Reported duration is one to four weeks. This image was taken at a distance. The lesion involves the arm, back of the hand and leg. The contributor is 40–49, male. Reported lesion symptoms include itching and bothersome appearance. Texture is reported as rough or flaky and raised or bumpy. The patient described the issue as a rash:
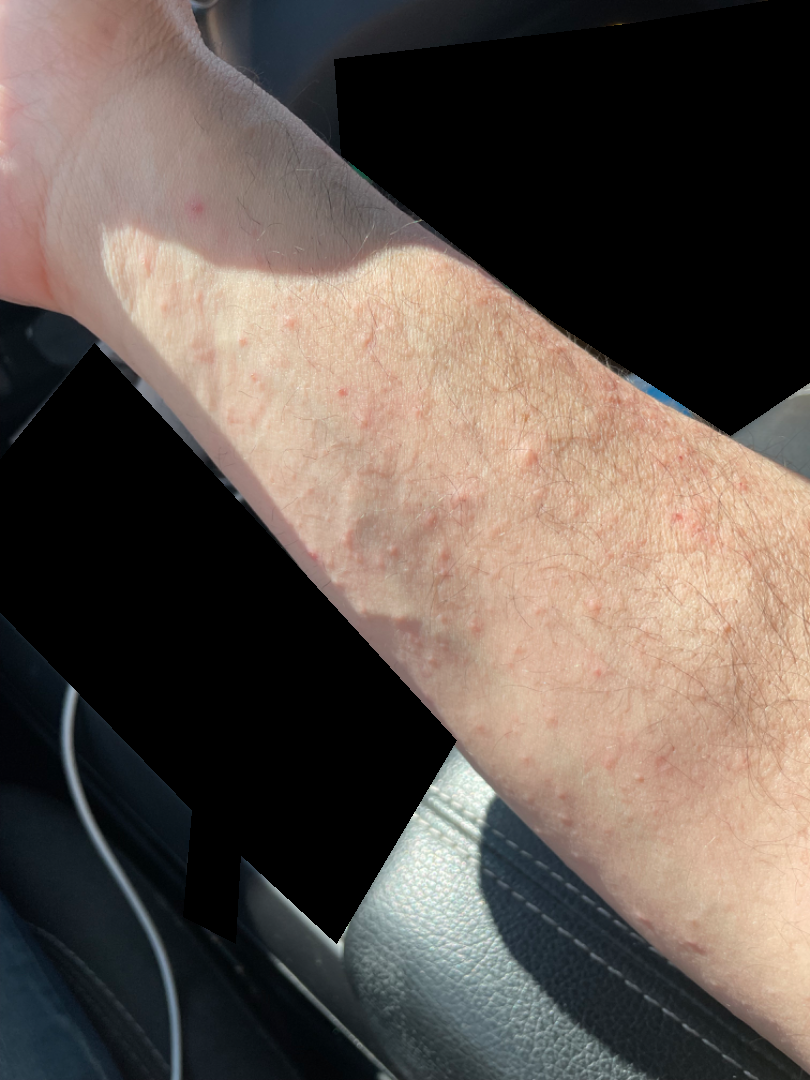dermatologist impression = Eczema (primary); Scabies (considered)